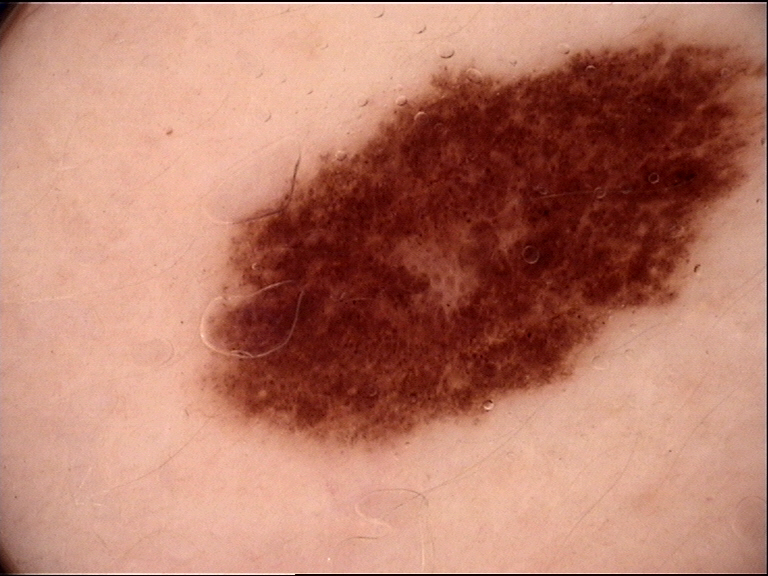Q: What is the imaging modality?
A: dermatoscopy
Q: What is this lesion?
A: dysplastic compound nevus (expert consensus)